Dermoscopy of a skin lesion: 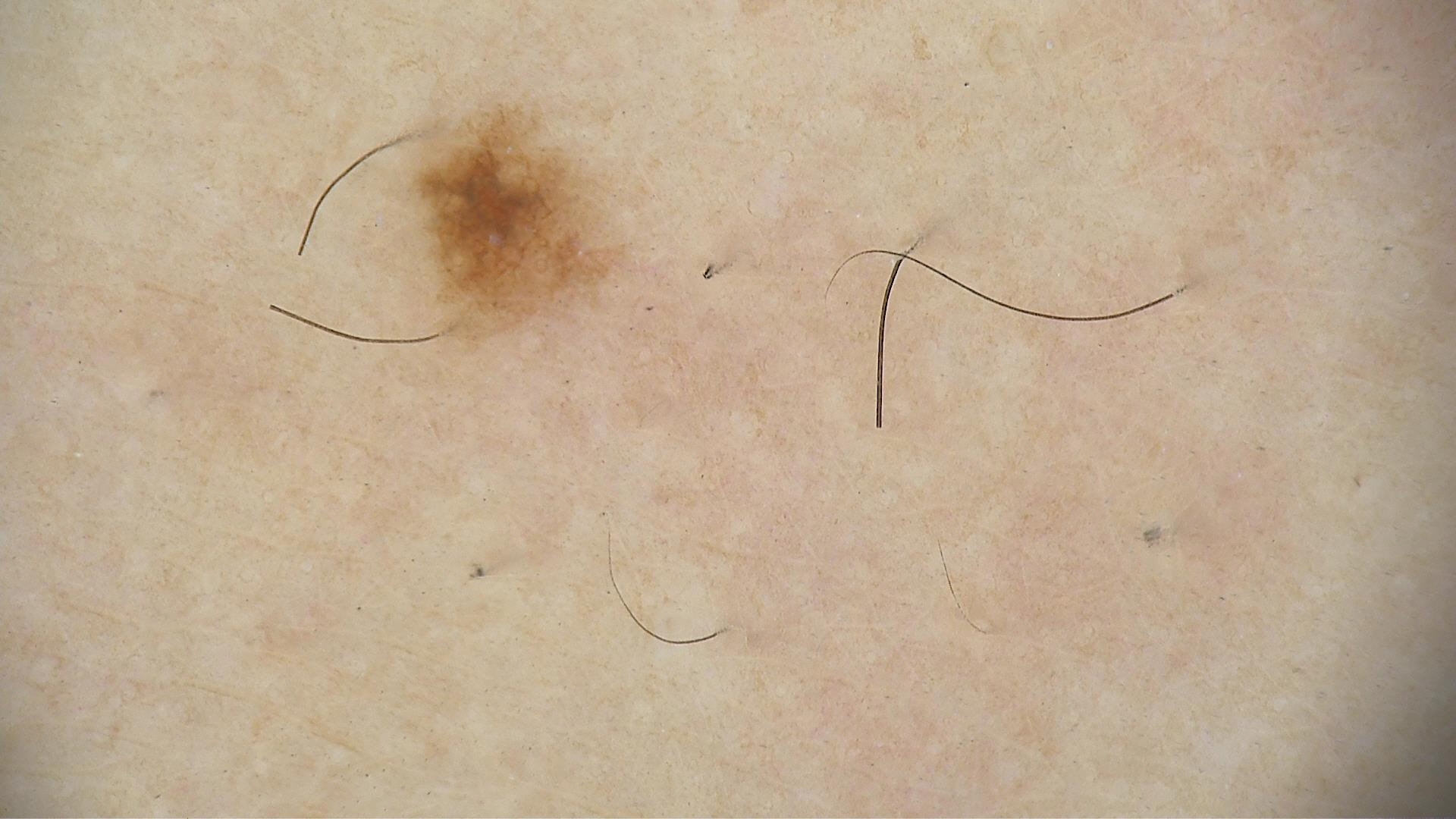class: dysplastic junctional nevus (expert consensus)